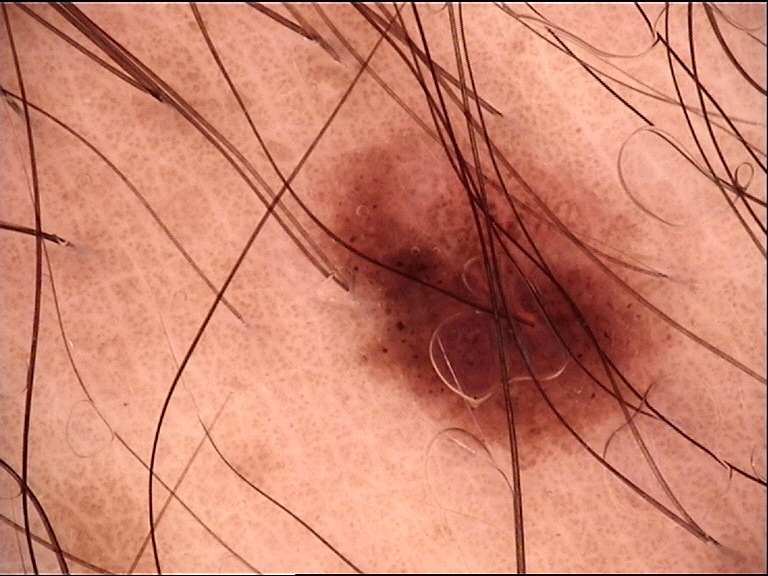A dermoscopy image of a single skin lesion. Diagnosed as a dysplastic junctional nevus.